A dermoscopy image of a single skin lesion.
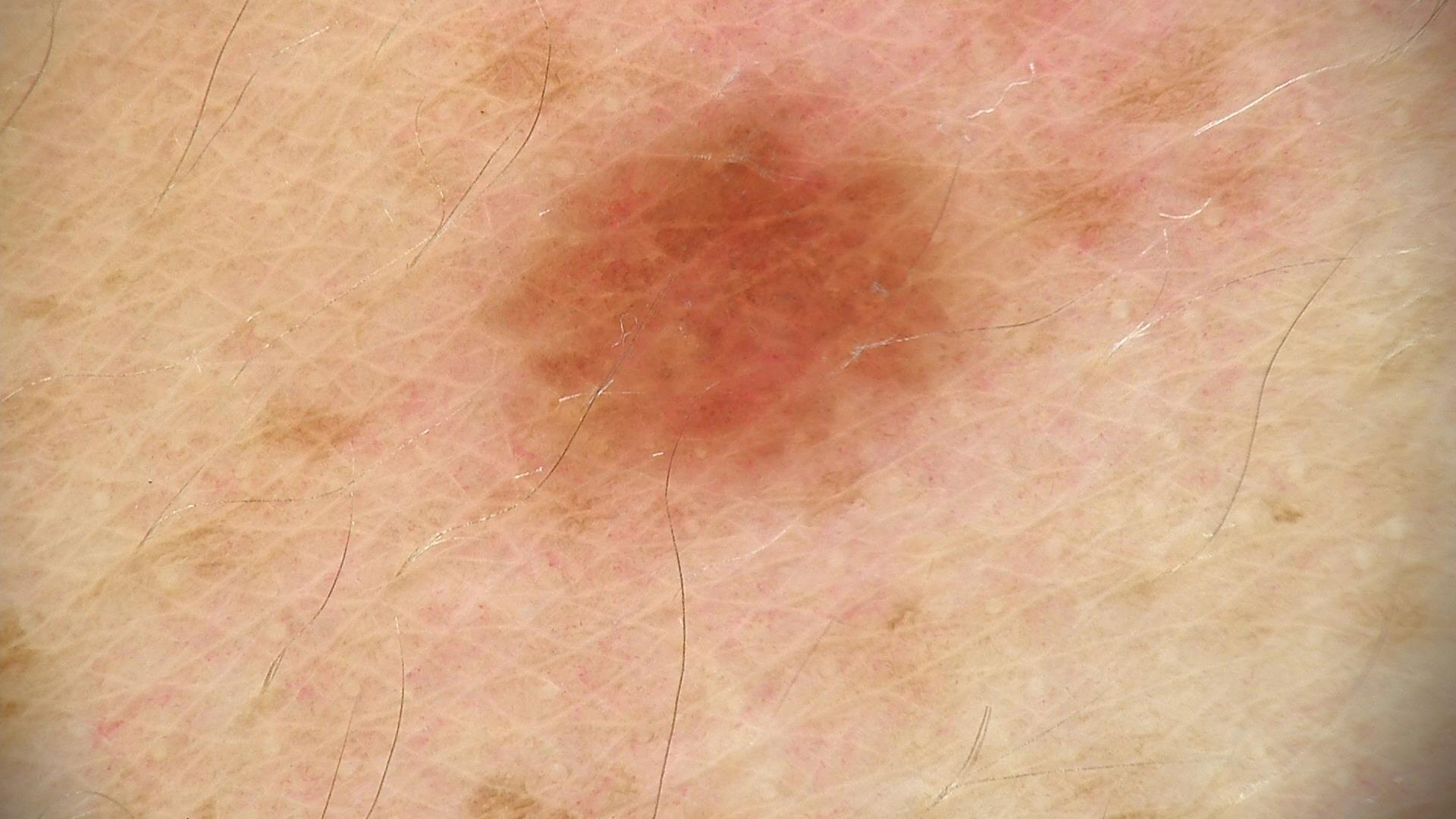Q: What is this lesion?
A: dysplastic junctional nevus (expert consensus)